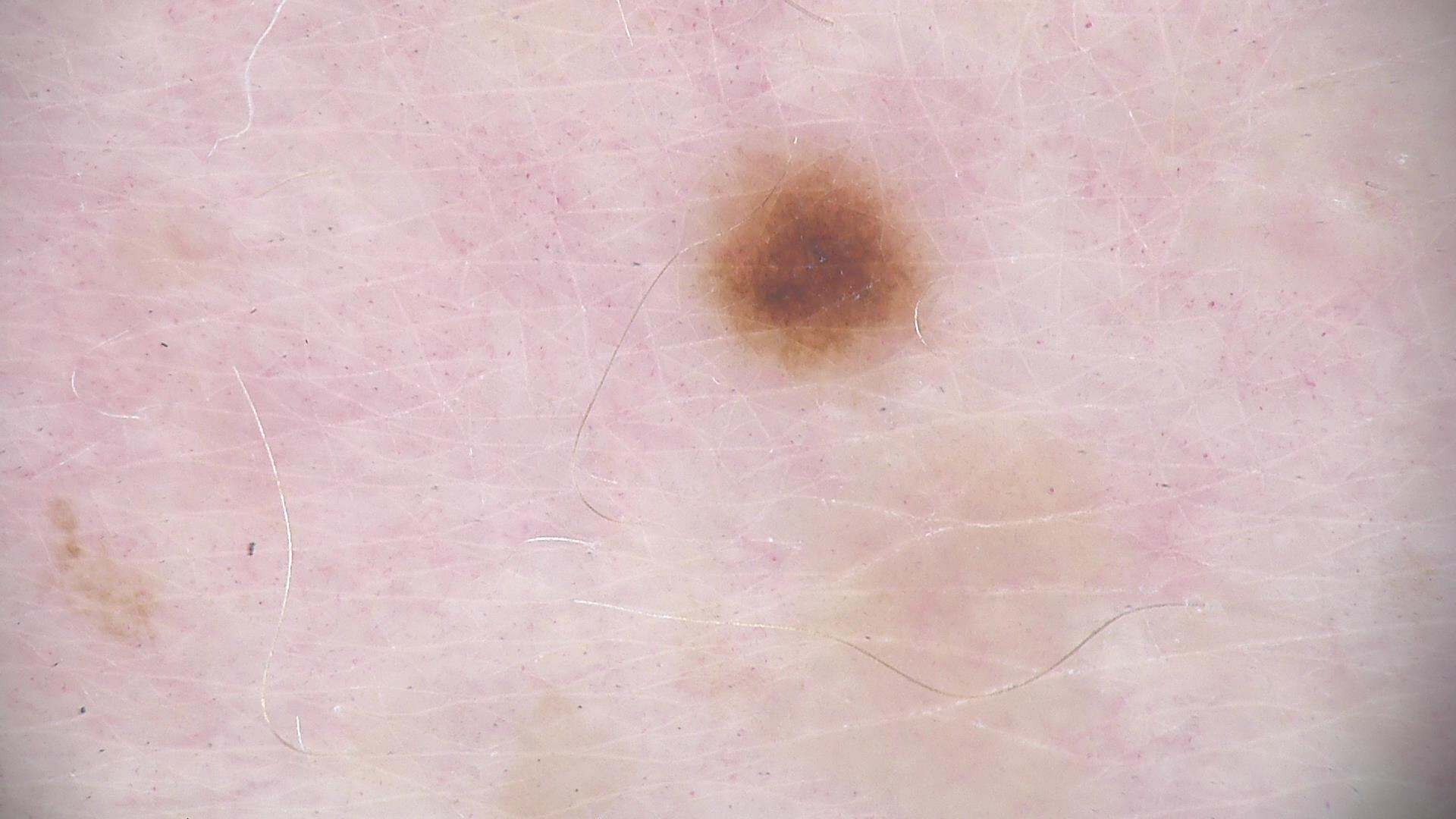A dermoscopy image of a single skin lesion.
The diagnostic label was a dysplastic junctional nevus.